This is a dermoscopic photograph of a skin lesion:
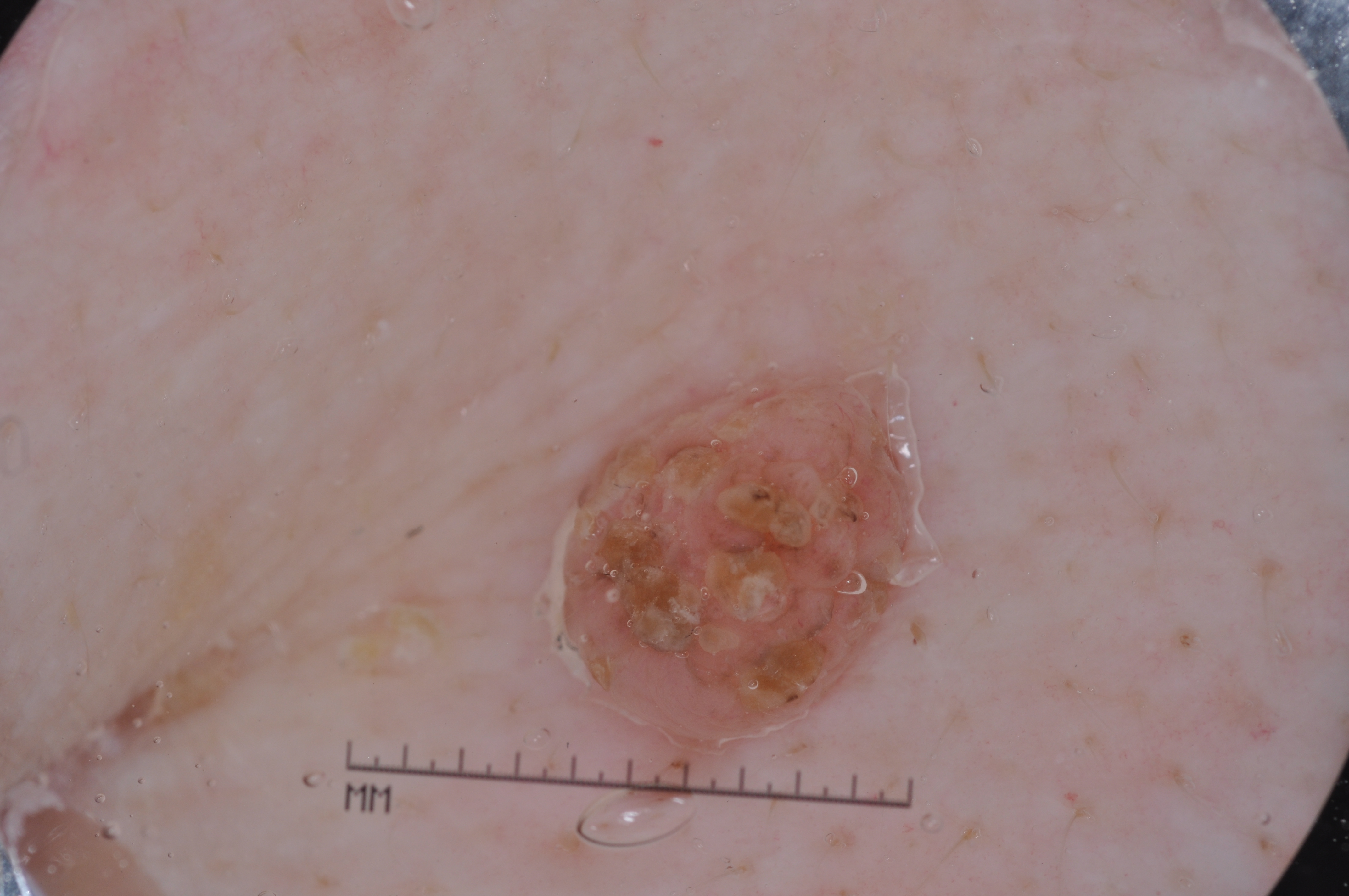The lesion takes up a moderate portion of the field.
Dermoscopically, the lesion shows no negative network, pigment network, milia-like cysts, or streaks.
In (x1, y1, x2, y2) order, lesion location: <bbox>551, 350, 936, 759</bbox>.
Consistent with a melanocytic nevus.